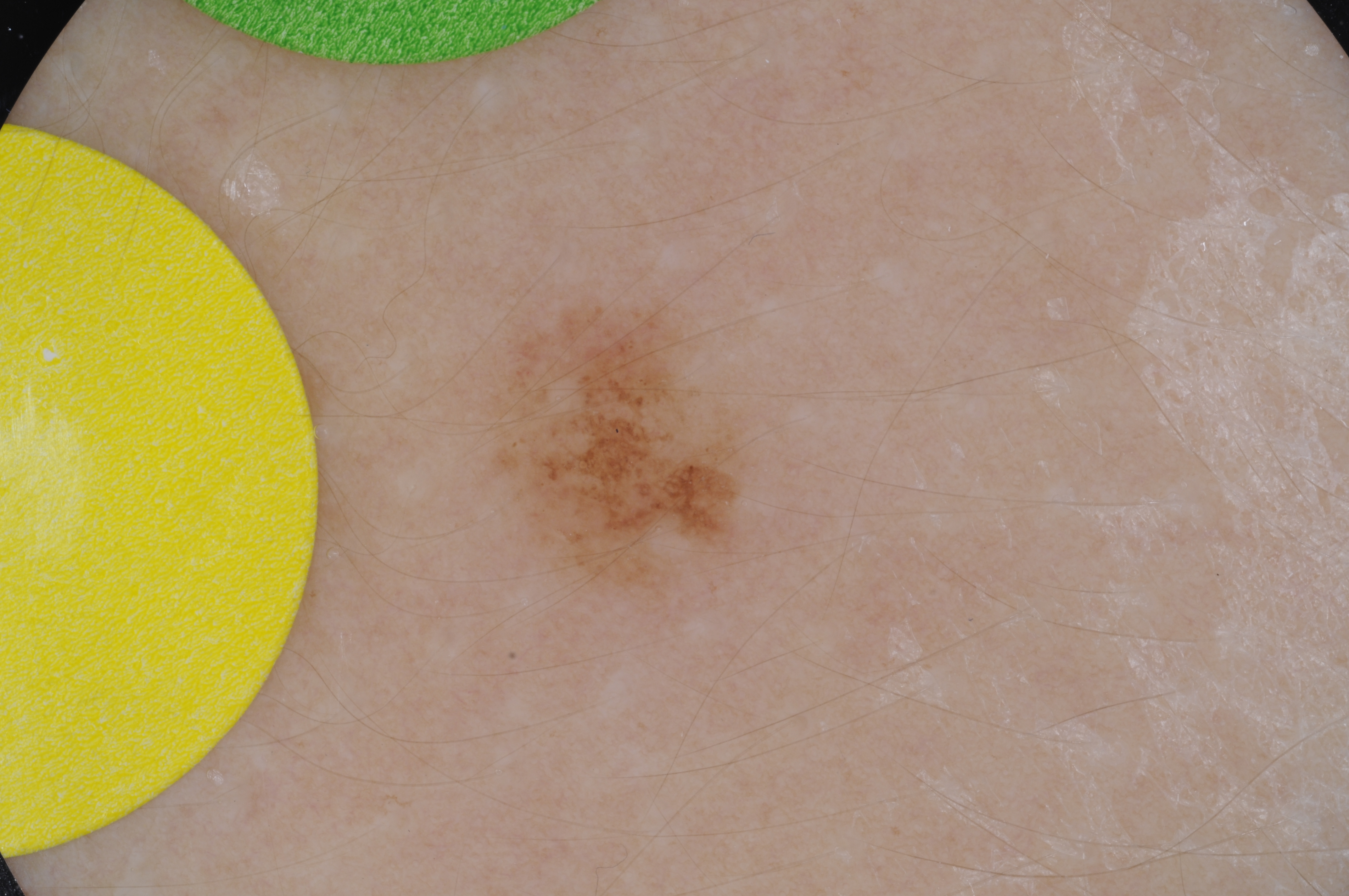Findings:
The subject is a male roughly 15 years of age. A dermoscopic close-up of a skin lesion. On dermoscopy, the lesion shows pigment network, with no milia-like cysts, globules, negative network, or streaks. With coordinates (x1, y1, x2, y2), the lesion's extent is [481, 288, 761, 611]. The lesion covers approximately 6% of the dermoscopic field.
Impression:
Expert review diagnosed this as a melanocytic nevus, a benign skin lesion.